A dermoscopic close-up of a skin lesion.
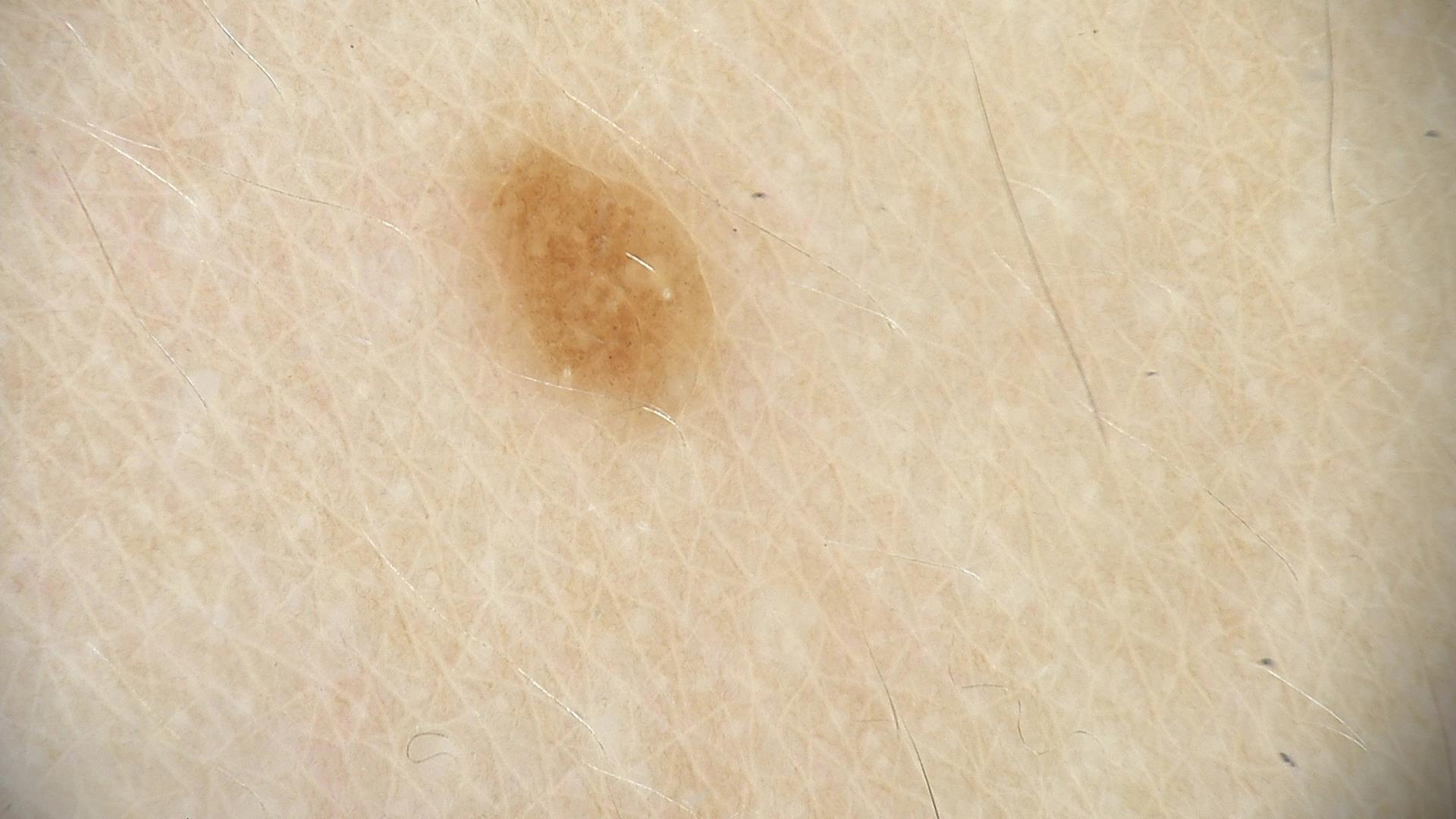label: dysplastic junctional nevus (expert consensus).